This image was taken at an angle; reported duration is three to twelve months; reported lesion symptoms include enlargement, pain, itching, burning, bleeding, bothersome appearance and darkening; the patient indicates associated fatigue and joint pain; located on the leg; the patient indicates the lesion is raised or bumpy, rough or flaky and fluid-filled; skin tone: non-clinician graders estimated a Monk Skin Tone of 2.
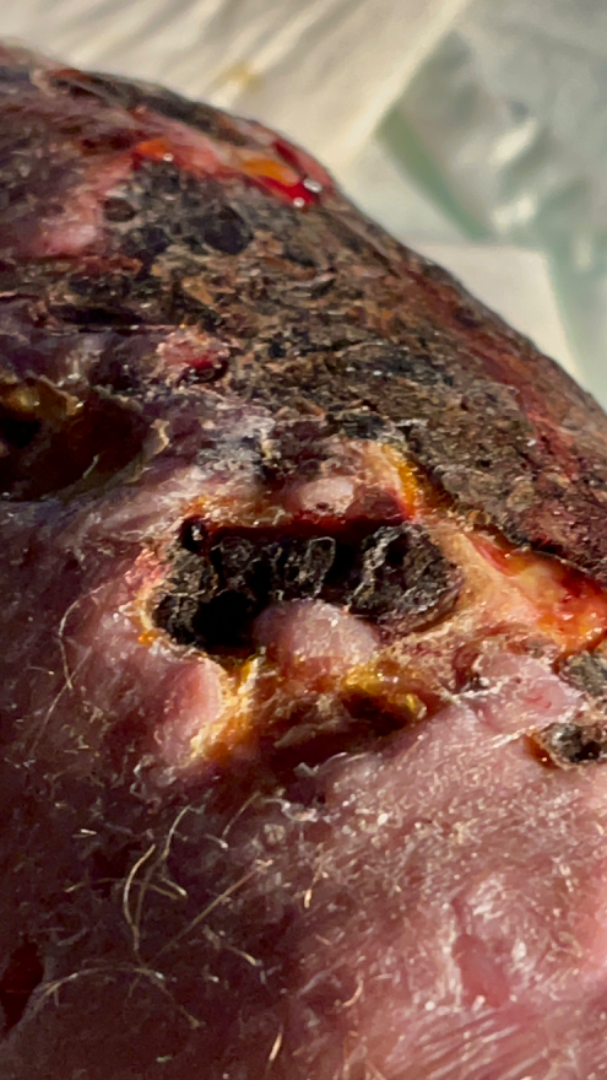{"assessment": "indeterminate"}